Imaged for a research study, with no referral diagnosis recorded; a female subject age 50; a dermoscopic image of a skin lesion; a moderate number of moles by the patient's own estimate.
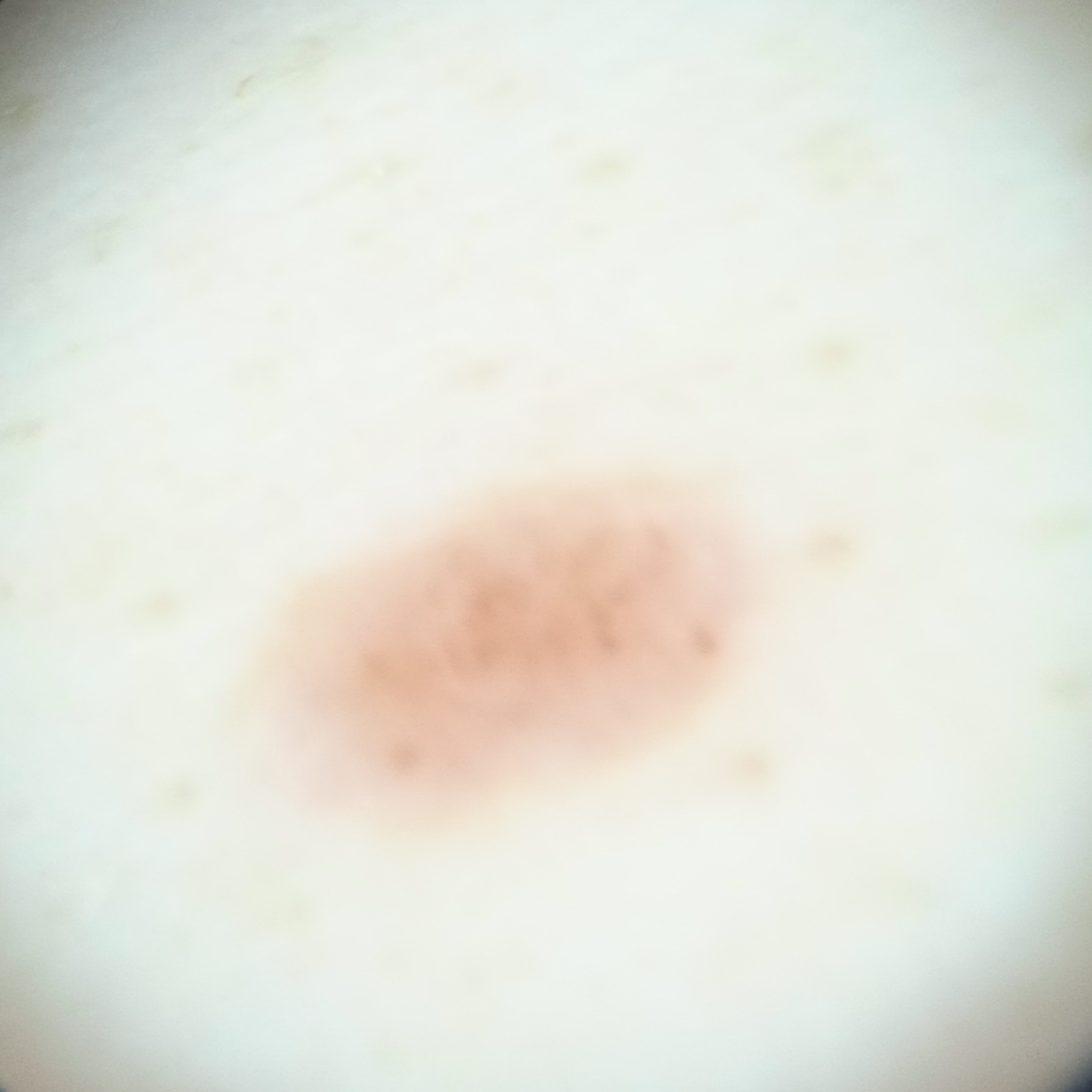Q: Where is the lesion?
A: the torso
Q: Lesion size?
A: 4.9 mm
Q: What was the diagnosis?
A: melanocytic nevus (dermatologist consensus)